This image was taken at a distance: 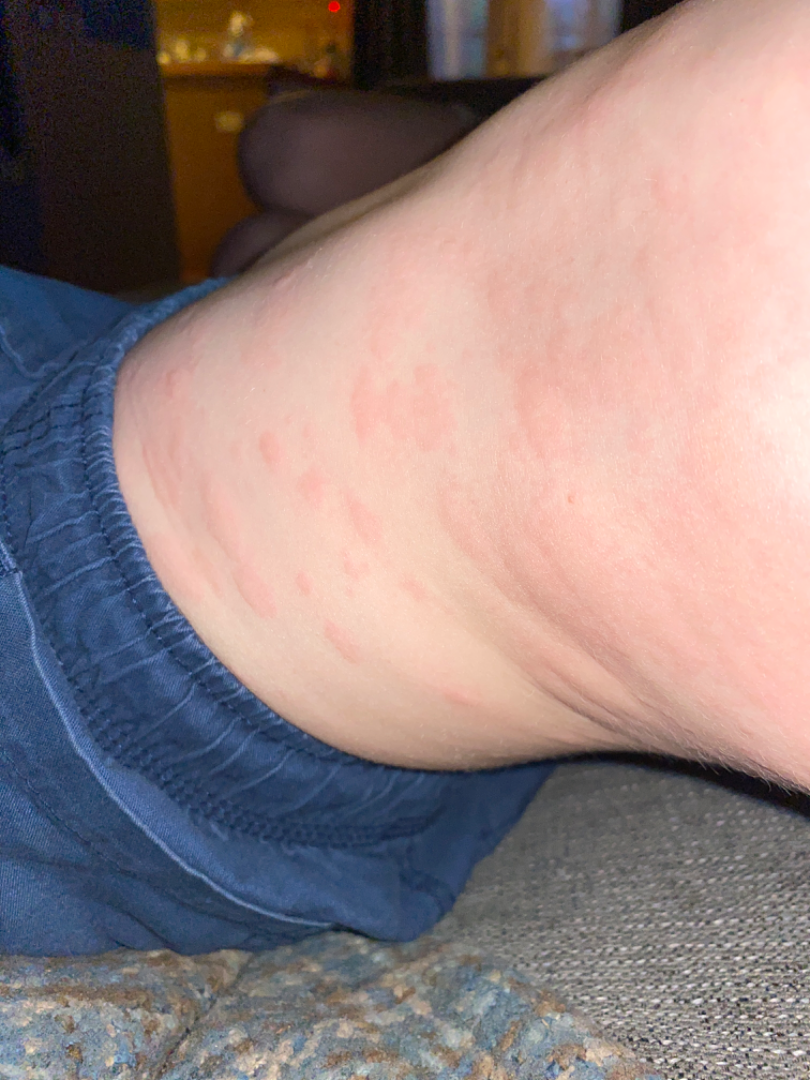Impression:
Reviewed remotely by one dermatologist: the impression is Urticaria.